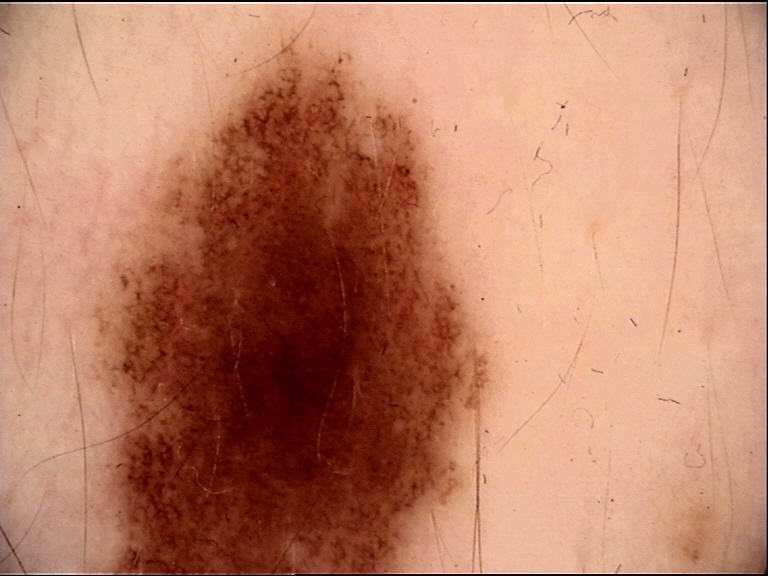image type — dermatoscopy
diagnostic label — dysplastic junctional nevus (expert consensus)